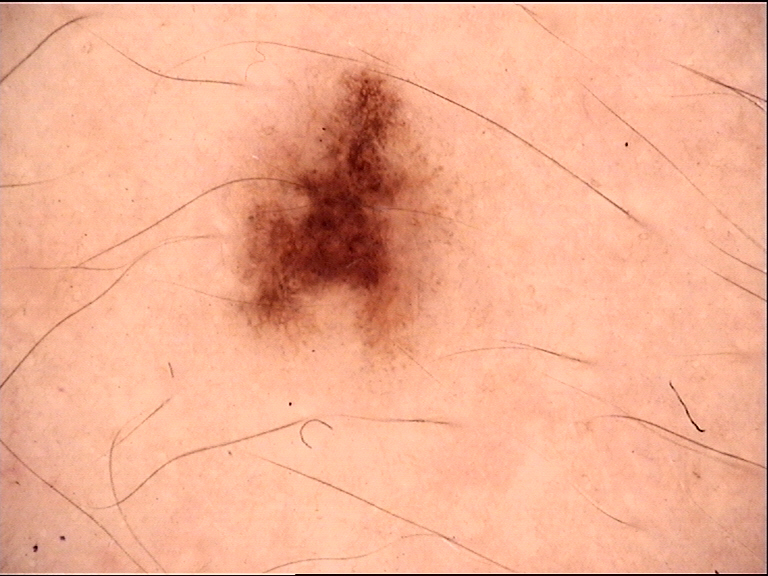A dermoscopic close-up of a skin lesion. Consistent with a benign lesion — a dysplastic junctional nevus.